A dermoscopic photograph of a skin lesion.
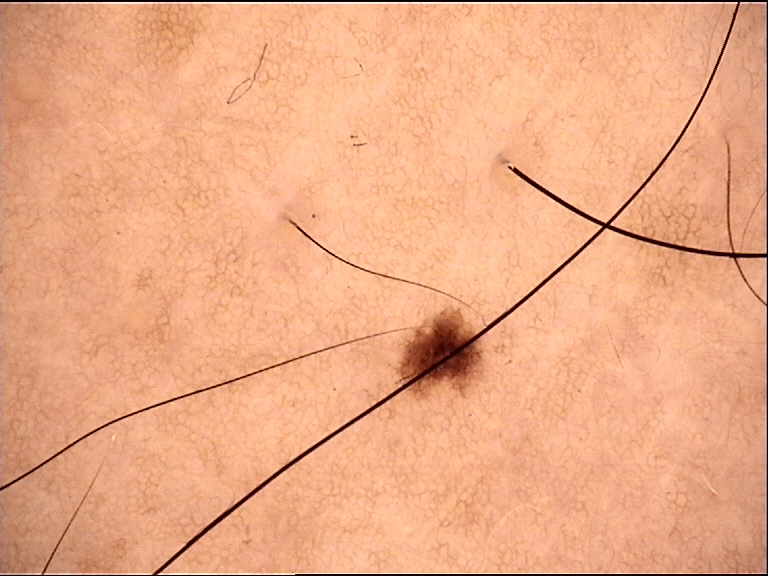Findings:
This is a banal lesion.
Conclusion:
Consistent with a junctional nevus.